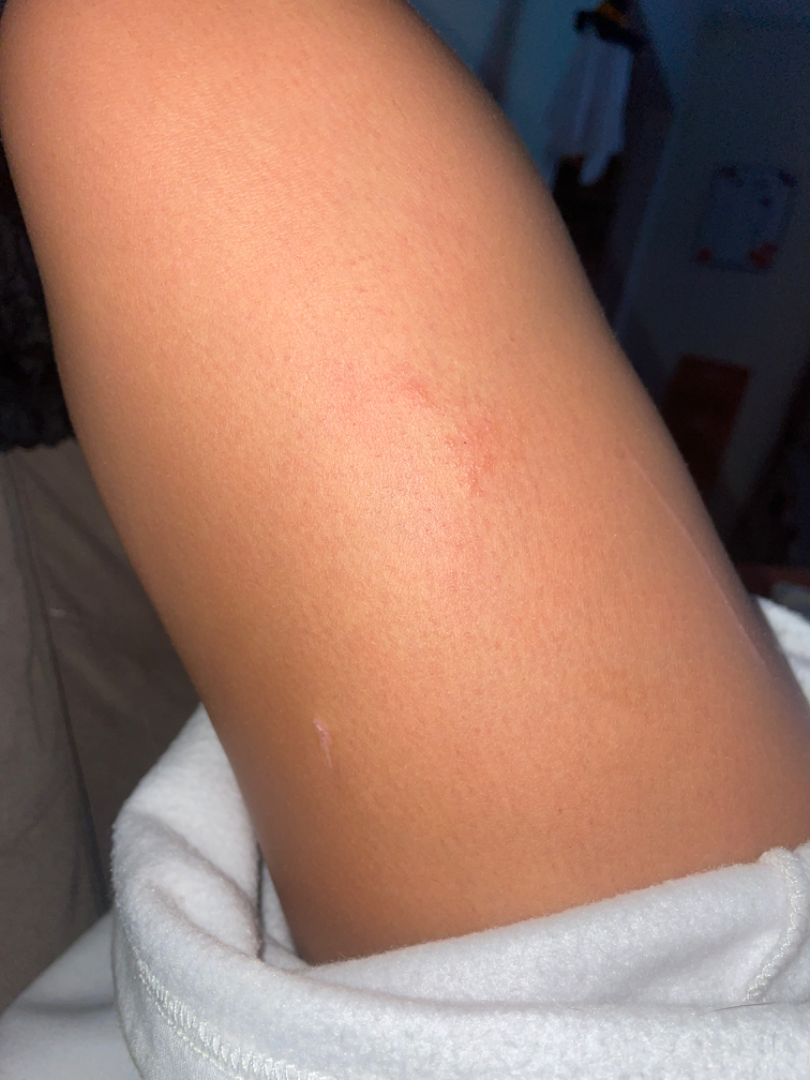texture: raised or bumpy
symptoms: none reported
patient_category: a rash
skin_tone:
  fitzpatrick: V
shot_type: at a distance
body_site: leg
differential:
  Allergic Contact Dermatitis: 0.67
  Eczema: 0.33